Recorded as skin type III · the chart notes tobacco use · a female subject 65 years of age · a clinical photo of a skin lesion taken with a smartphone: 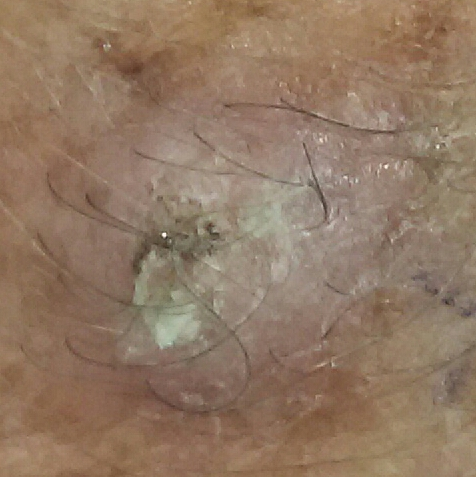Findings:
The patient reports that the lesion is elevated and itches.
Conclusion:
Biopsy-confirmed as a squamous cell carcinoma.